A dermatoscopic image of a skin lesion:
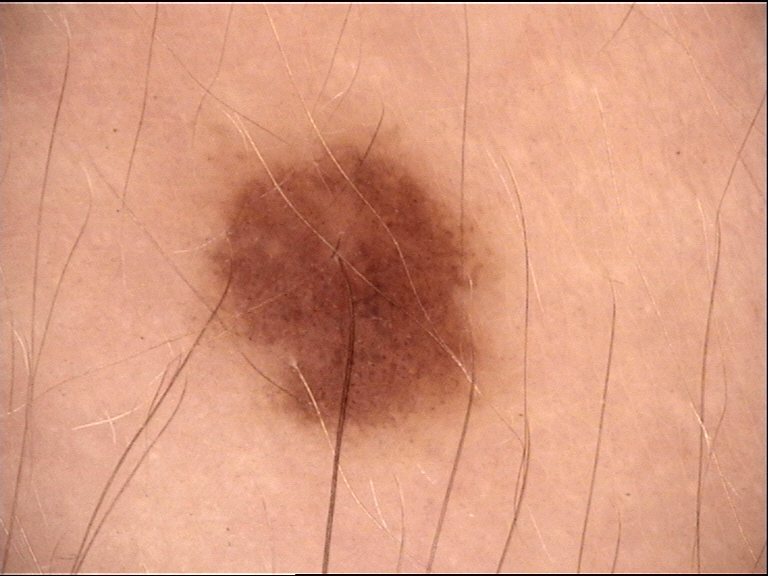Labeled as a banal lesion — a junctional nevus.